A dermoscopic photograph of a skin lesion: 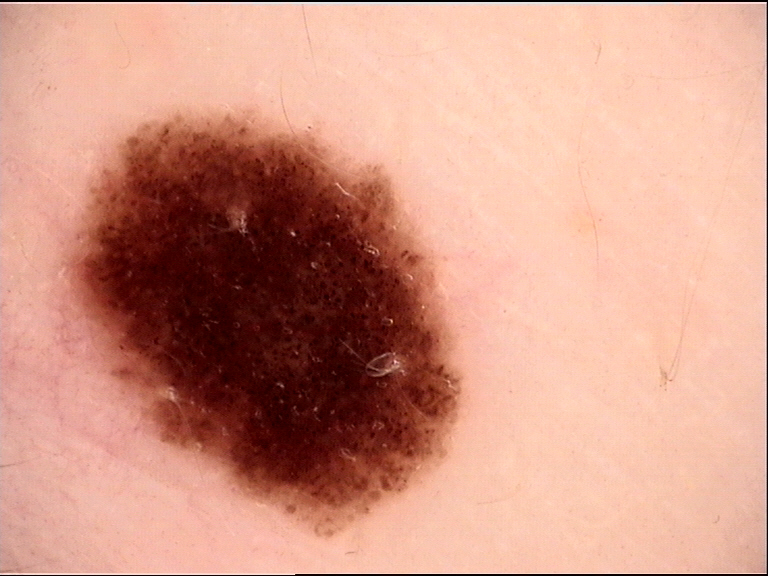Consistent with a benign lesion — a dysplastic compound nevus.